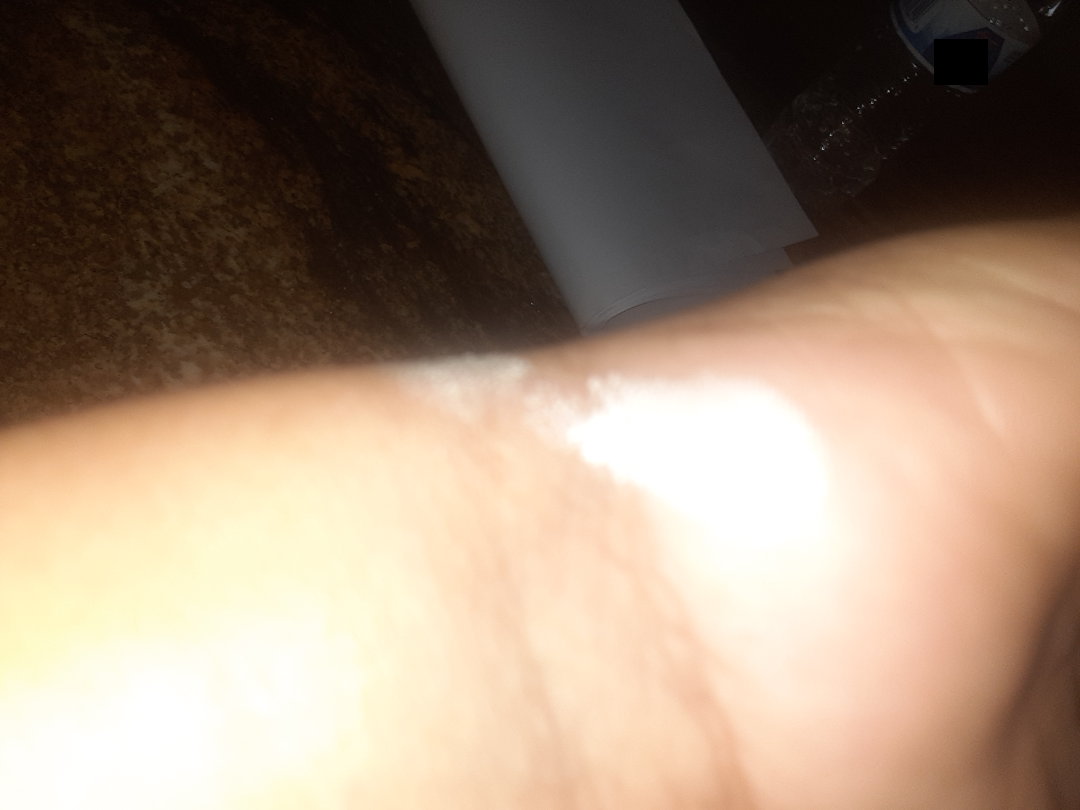assessment: indeterminate from the photograph.